A male patient, aged 58-62. A dermoscopic close-up of a skin lesion.
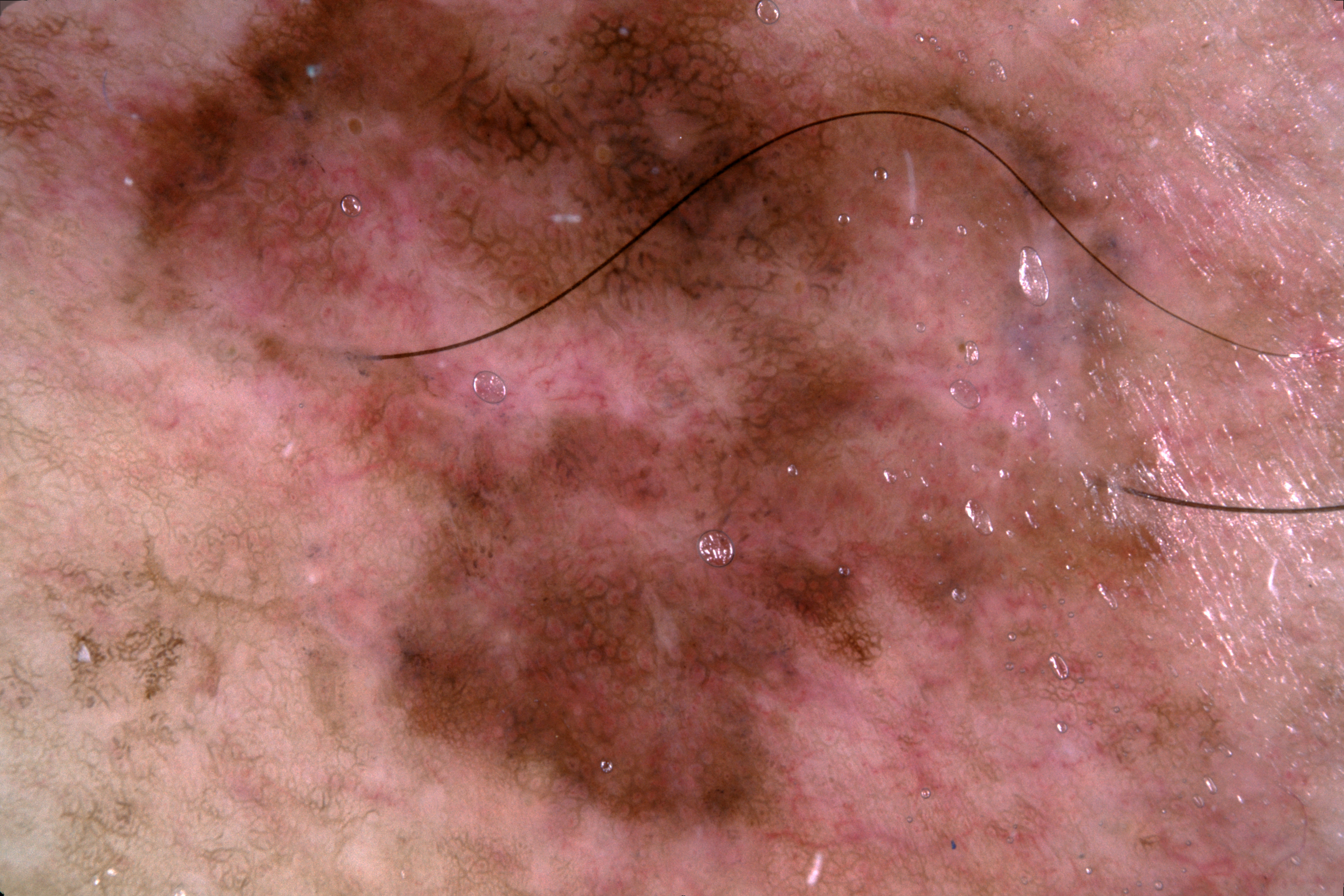<case>
  <dermoscopic_features>
    <present>pigment network</present>
    <absent>milia-like cysts, streaks, negative network</absent>
  </dermoscopic_features>
  <frame_clip>lesion extends past the field edge</frame_clip>
  <lesion_location>
    <bbox_xyxy>105, 0, 1239, 895</bbox_xyxy>
  </lesion_location>
  <lesion_extent>
    <approx_field_fraction_pct>66</approx_field_fraction_pct>
  </lesion_extent>
  <diagnosis>
    <name>melanoma</name>
    <malignancy>malignant</malignancy>
    <lineage>melanocytic</lineage>
    <provenance>histopathology</provenance>
  </diagnosis>
</case>